The patient says their skin tans without first burning. Acquired for a research image collection, with no referral diagnosis. A dermoscopy image of a skin lesion. A moderate number of moles by the patient's own estimate. The patient reports a history of sunbed use. A female patient 47 years of age: 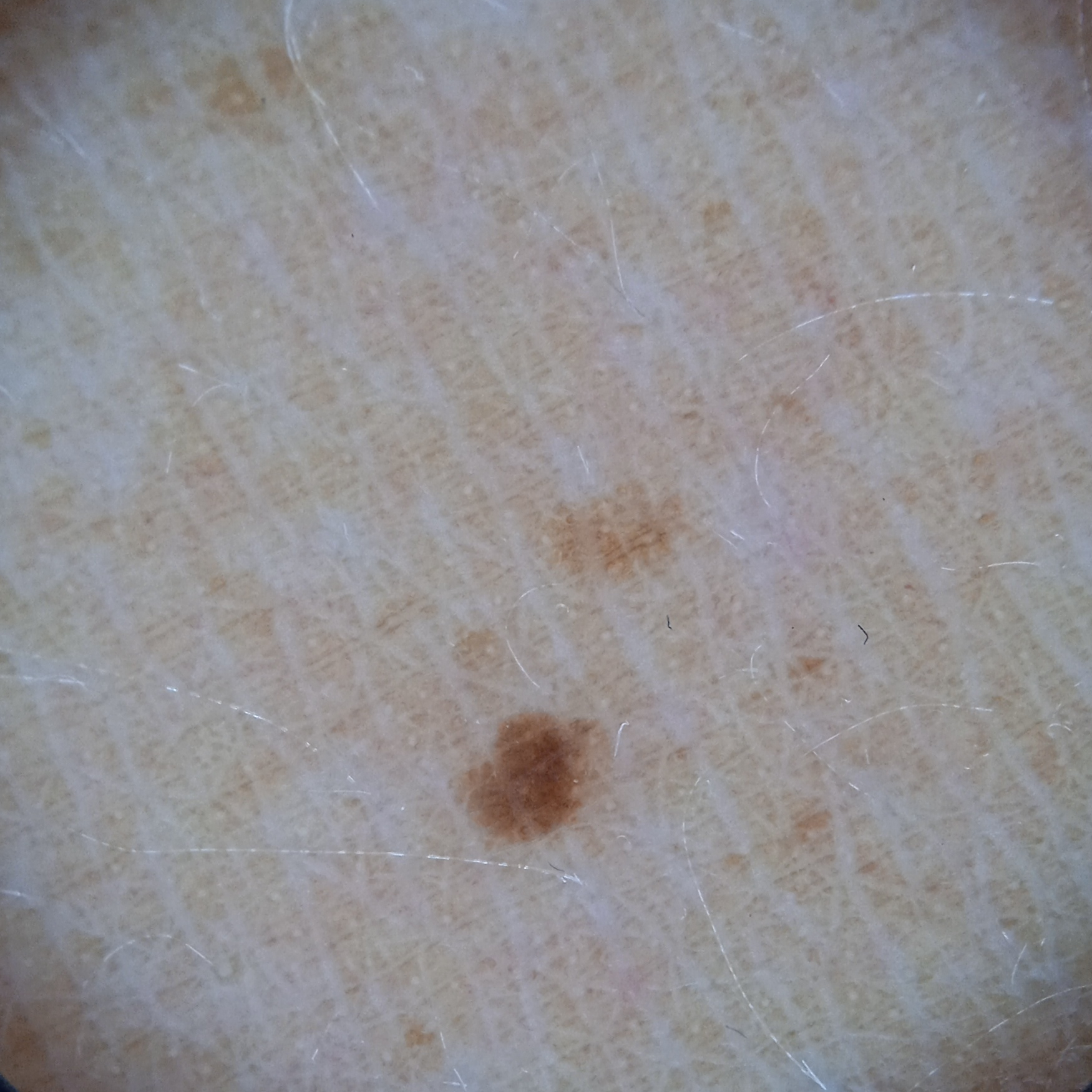Clinical context: The lesion is on the back. Measuring roughly 1.8 mm. Impression: The consensus diagnosis for this lesion was a melanocytic nevus.